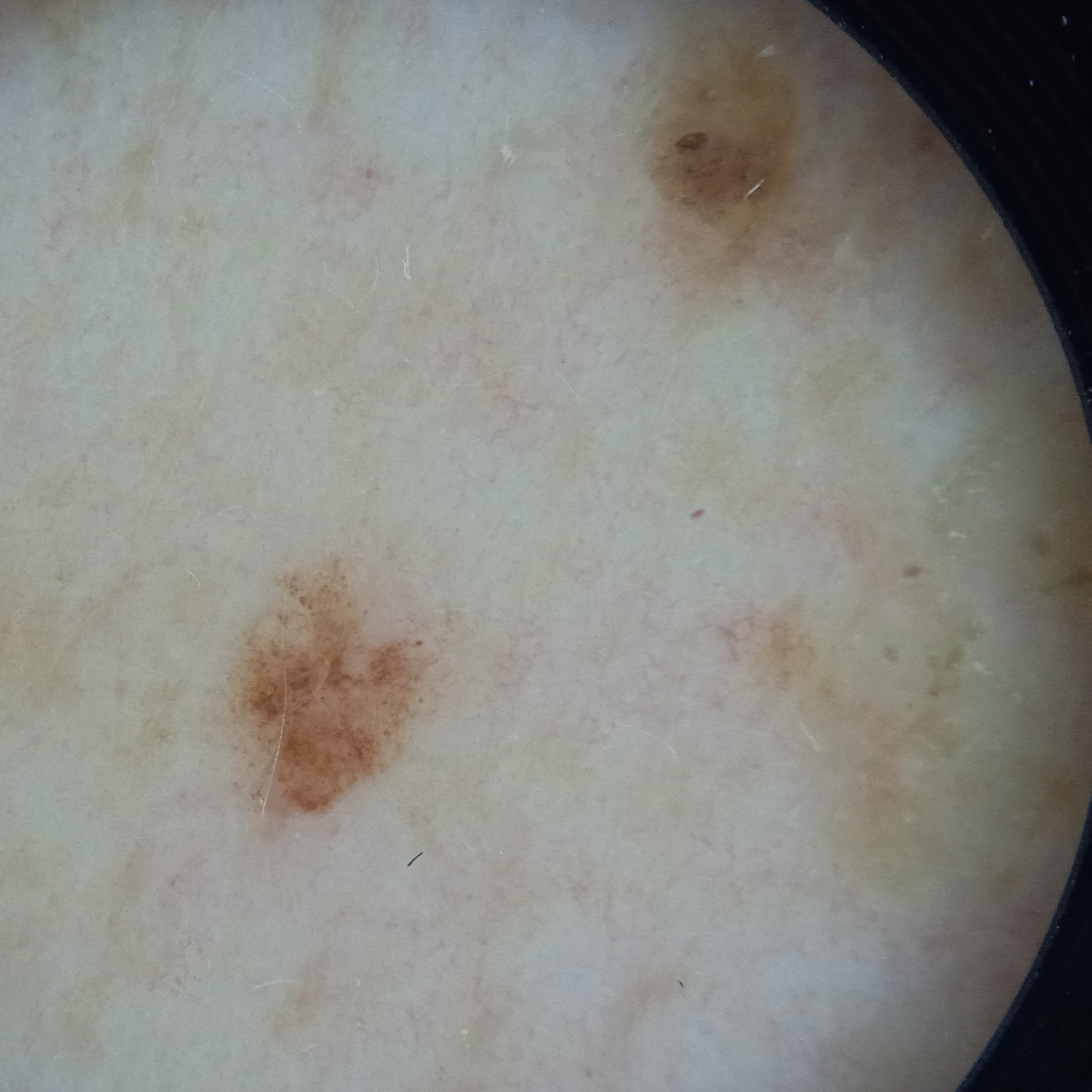Q: Why was this imaged?
A: research study (no referral diagnosis)
Q: What is the imaging modality?
A: dermoscopic image
Q: Where is the lesion?
A: the back
Q: How large is the lesion?
A: 3.1 mm
Q: What was the diagnosis?
A: seborrheic keratosis (dermatologist consensus)